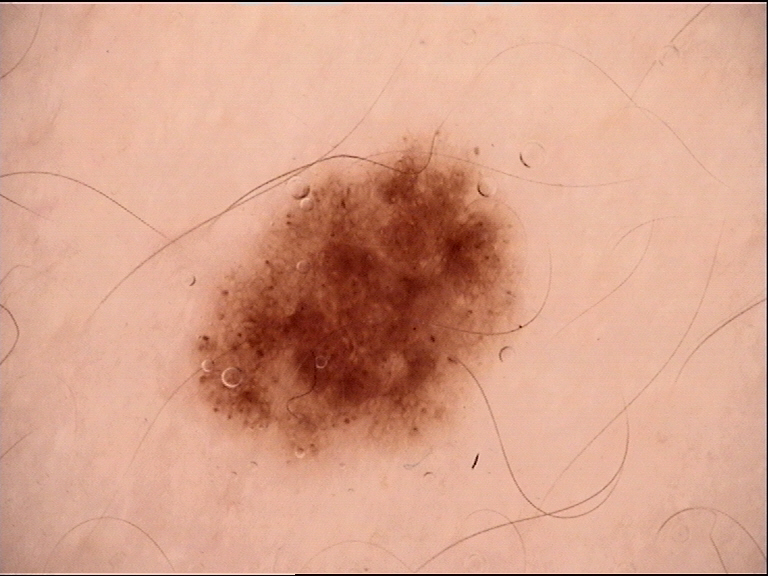– diagnostic label — dysplastic junctional nevus (expert consensus)